An image taken at an angle:
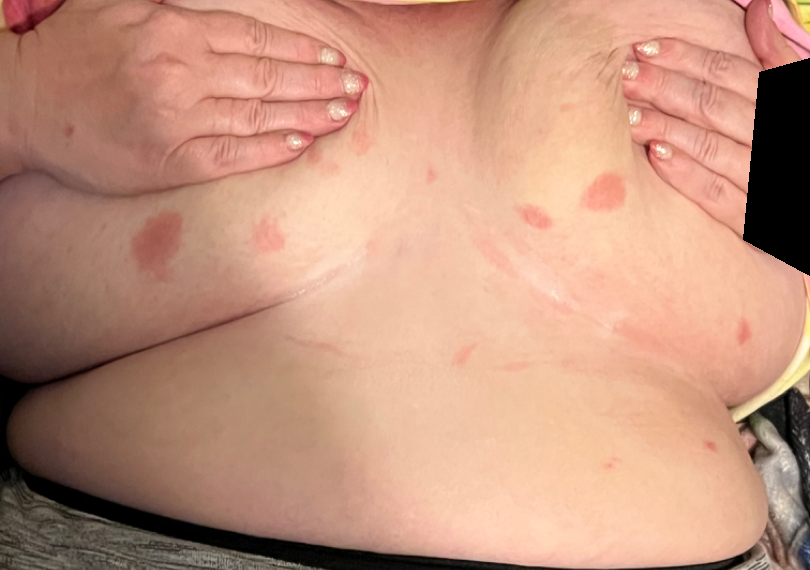On dermatologist assessment of the image, the differential is split between Pityriasis rosea, Psoriasis and Hypersensitivity.